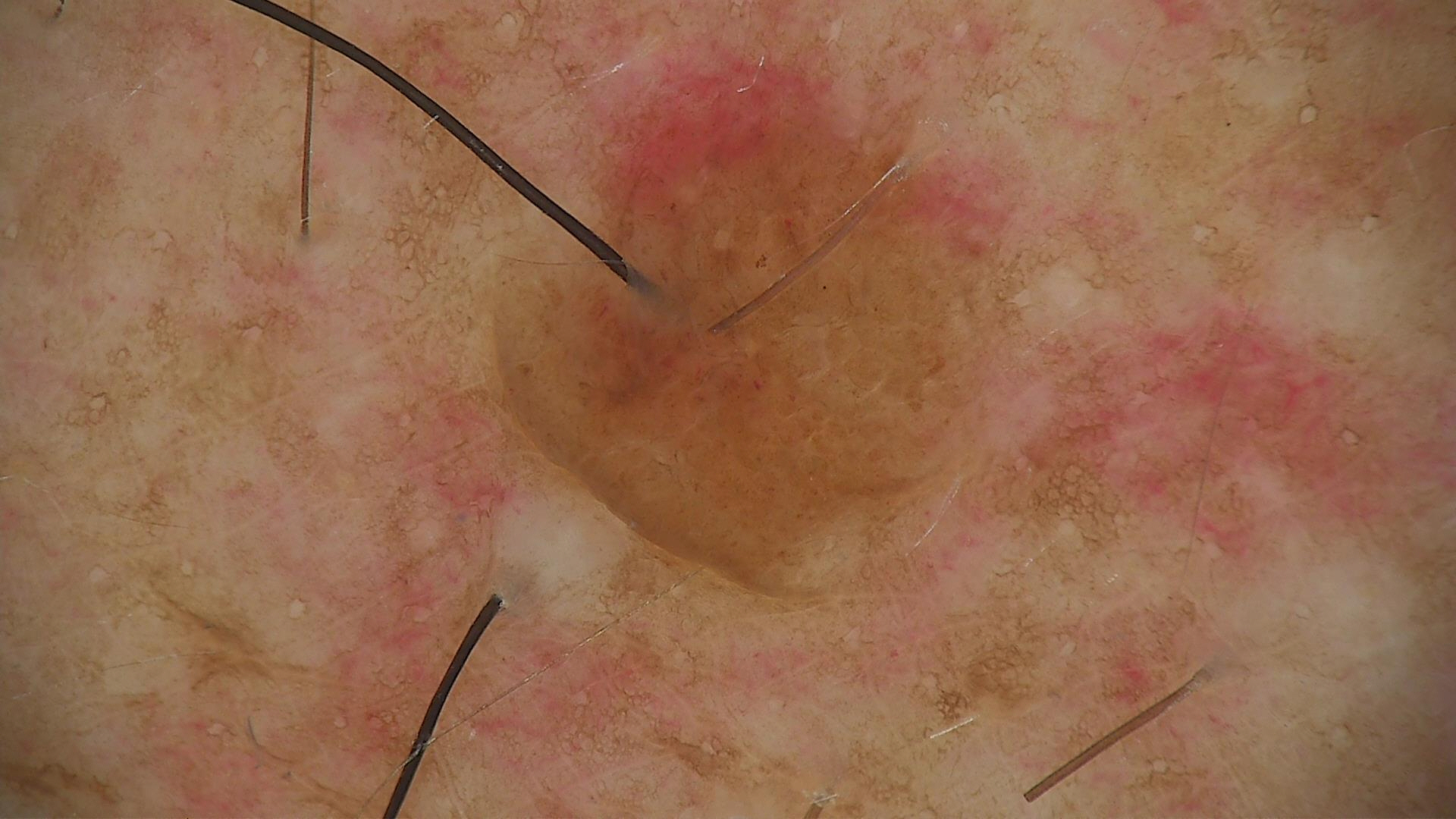Q: What kind of image is this?
A: dermoscopy
Q: How is the lesion classified?
A: banal
Q: What is this lesion?
A: dermal nevus (expert consensus)